A subject aged 71 · a clinical photograph of a skin lesion — 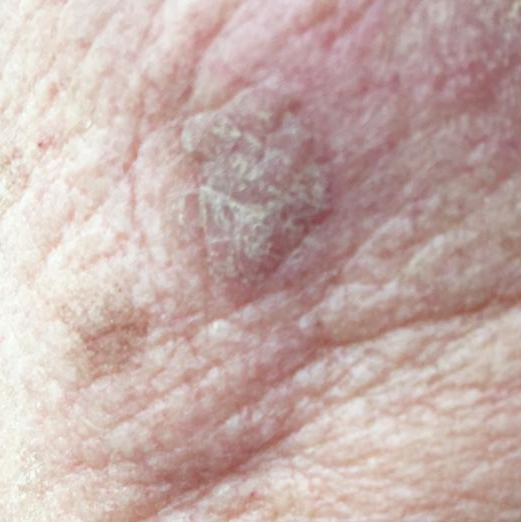| feature | finding |
|---|---|
| patient-reported symptoms | no bleeding |
| diagnosis | actinic keratosis (clinical consensus) |